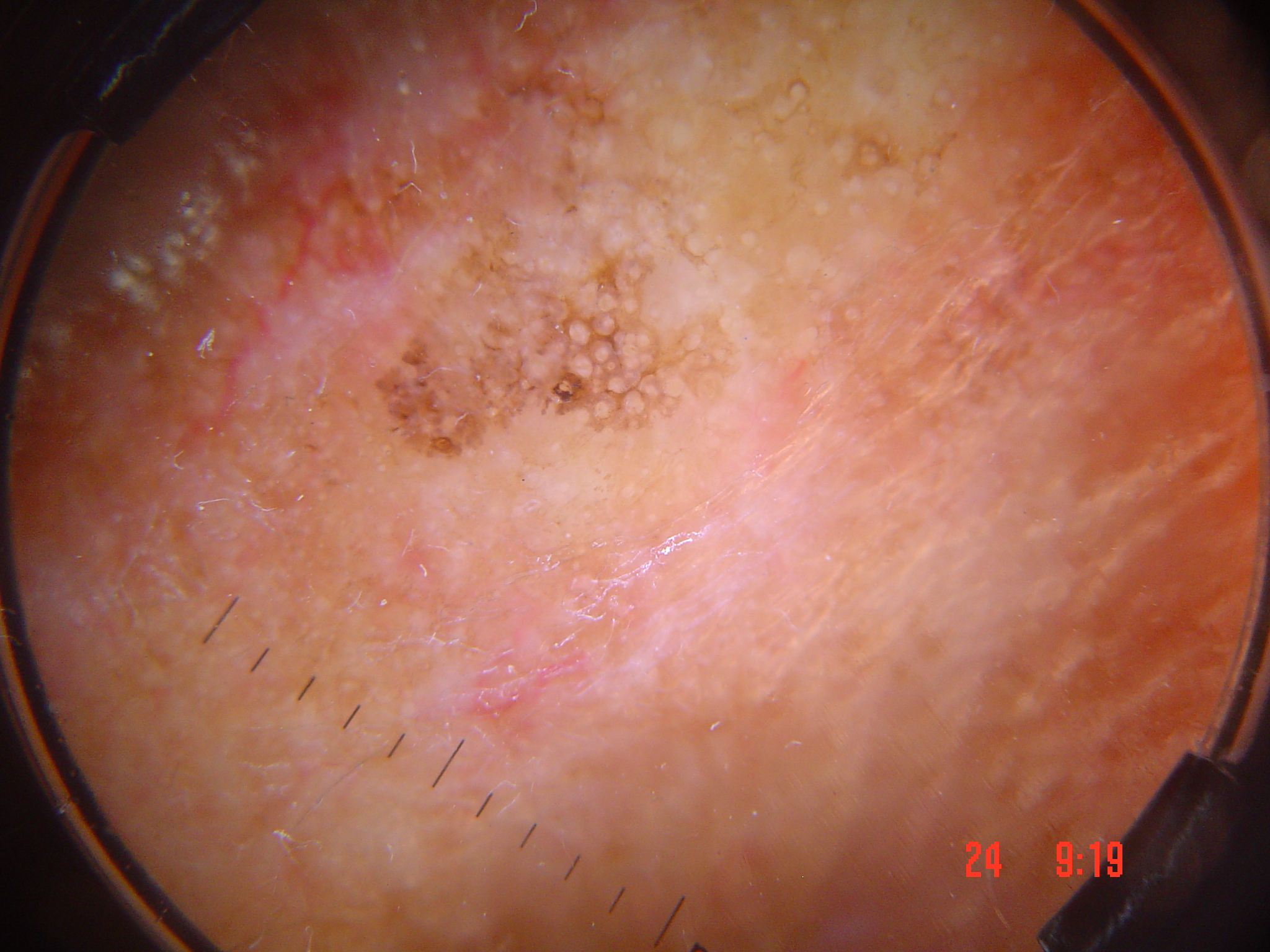Labeled as an actinic keratosis.